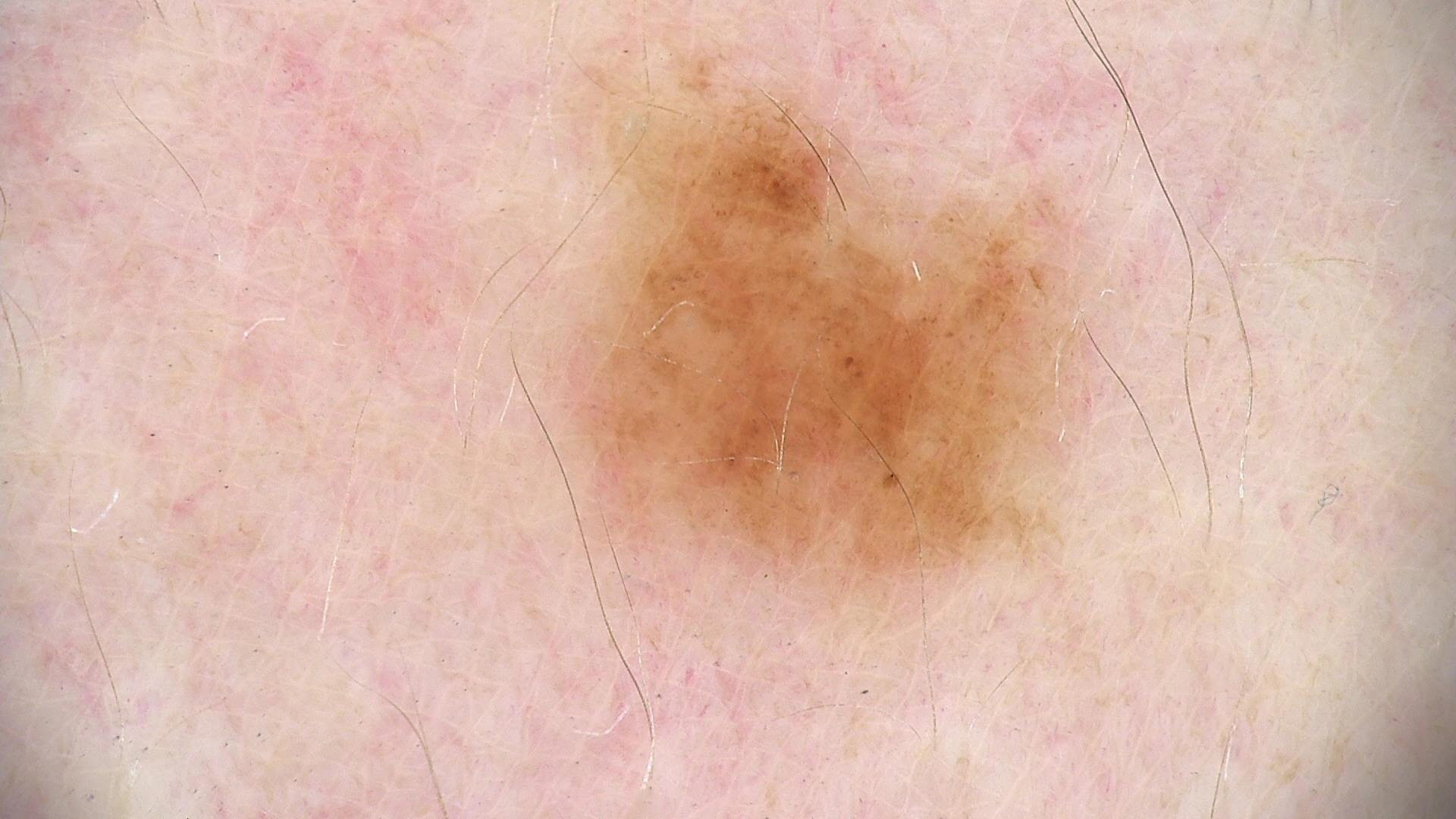diagnosis: dysplastic junctional nevus (expert consensus)